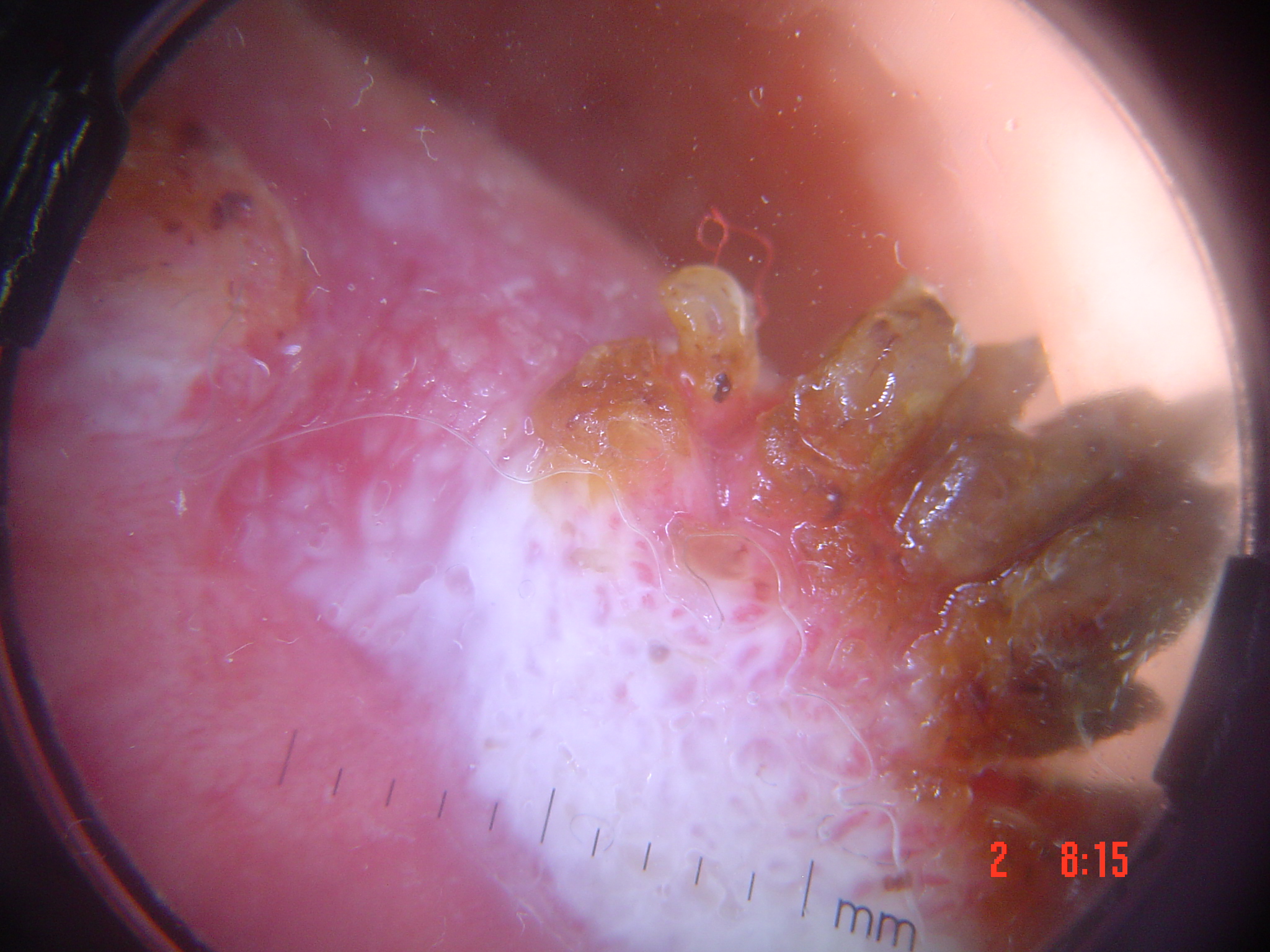Q: What did the workup show?
A: squamous cell carcinoma (biopsy-proven)